A close-up photograph · the back of the hand, arm, head or neck and palm are involved · texture is reported as flat and raised or bumpy · the subject is 30–39, male · the patient indicates the condition has been present for one to three months · reported lesion symptoms include itching and bothersome appearance.
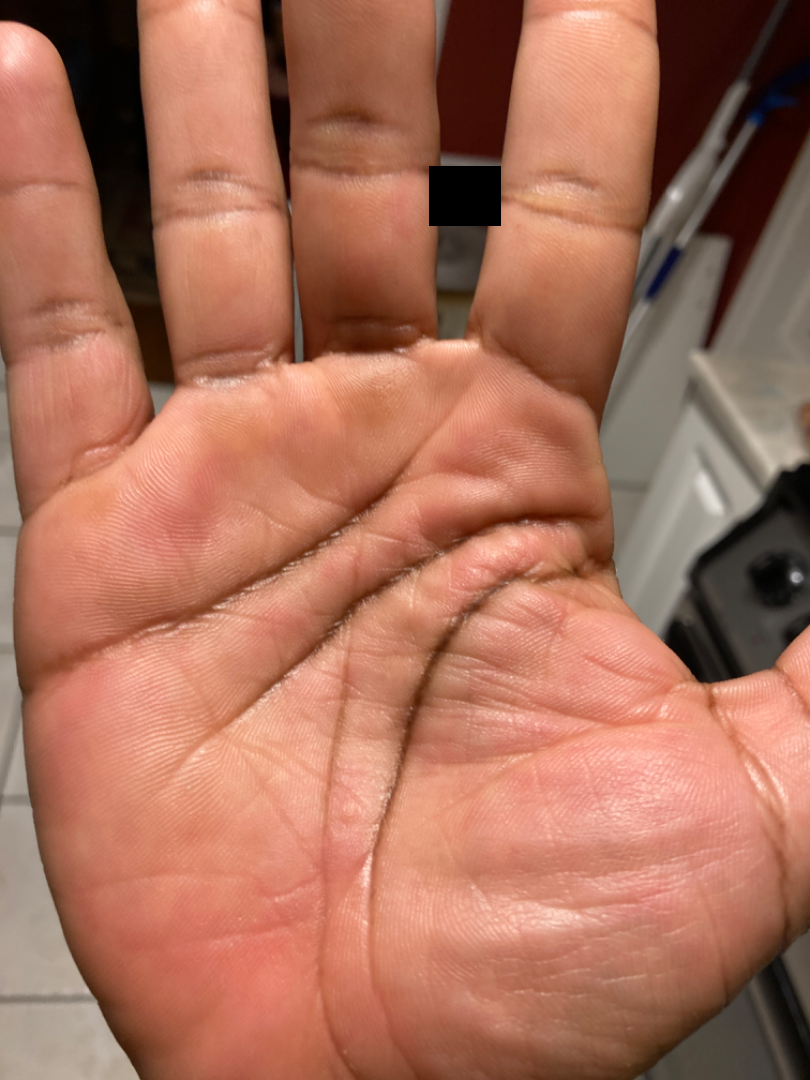Q: What was the assessment?
A: no skin condition identified